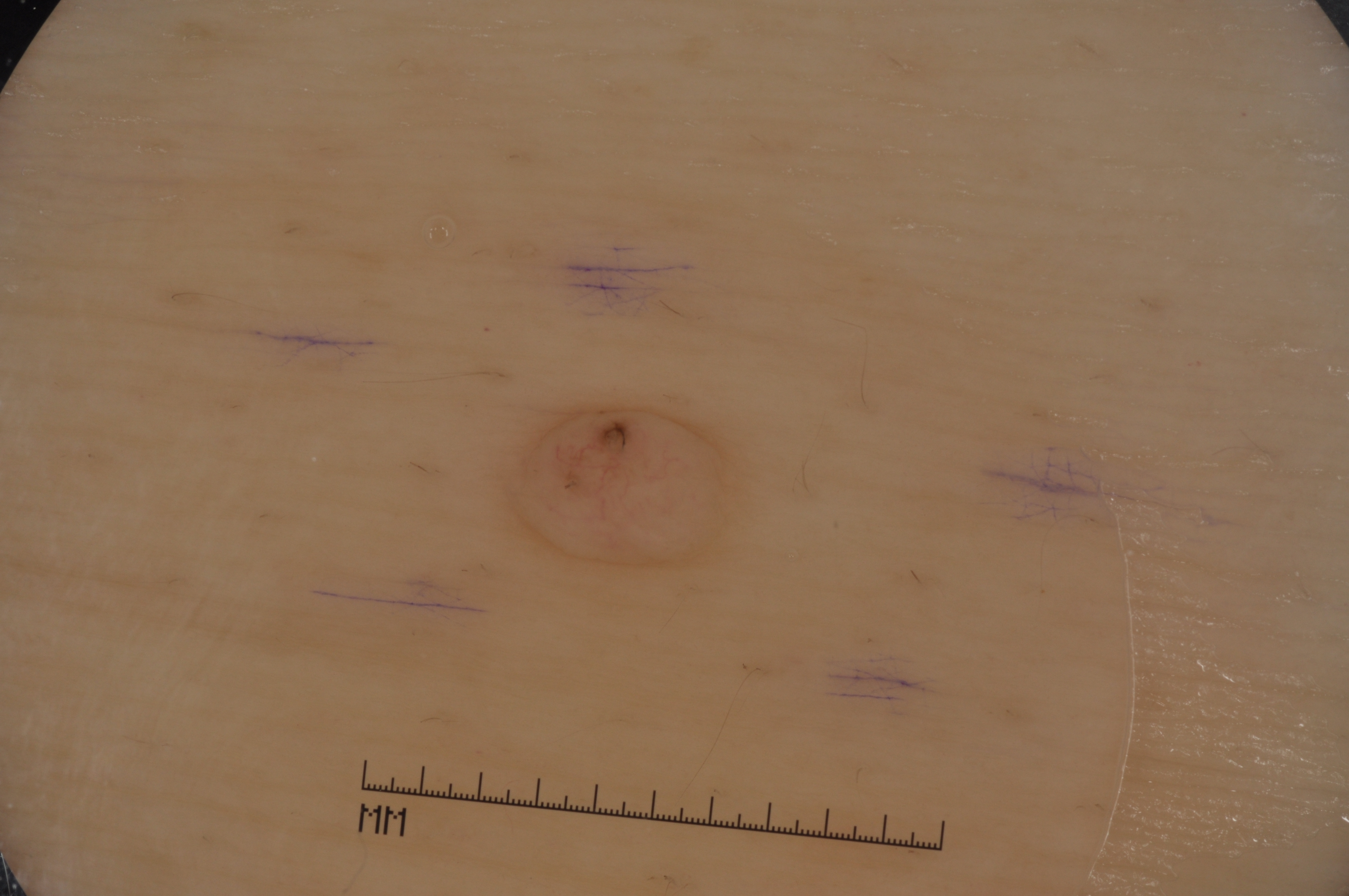Findings:
• imaging · dermoscopy of a skin lesion
• subject · female, in their mid- to late 60s
• bounding box · box(485, 393, 769, 588)
• absent dermoscopic findings · milia-like cysts, streaks, negative network, and pigment network
• diagnostic label · a melanocytic nevus, a benign lesion